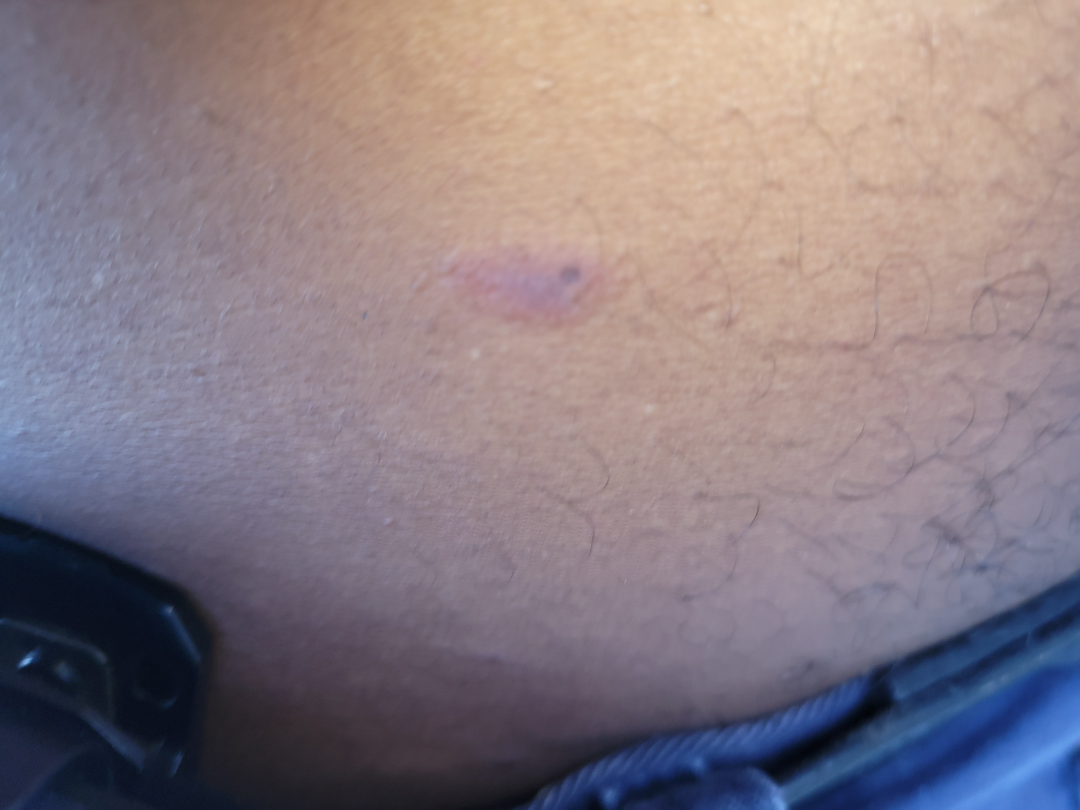{
  "texture": "raised or bumpy",
  "body_site": [
    "front of the torso",
    "arm",
    "leg"
  ],
  "duration": "one to four weeks",
  "systemic_symptoms": "none reported",
  "patient_category": "a rash",
  "symptoms": "itching",
  "shot_type": "close-up",
  "differential": {
    "leading": [
      "Pityriasis rosea"
    ]
  }
}